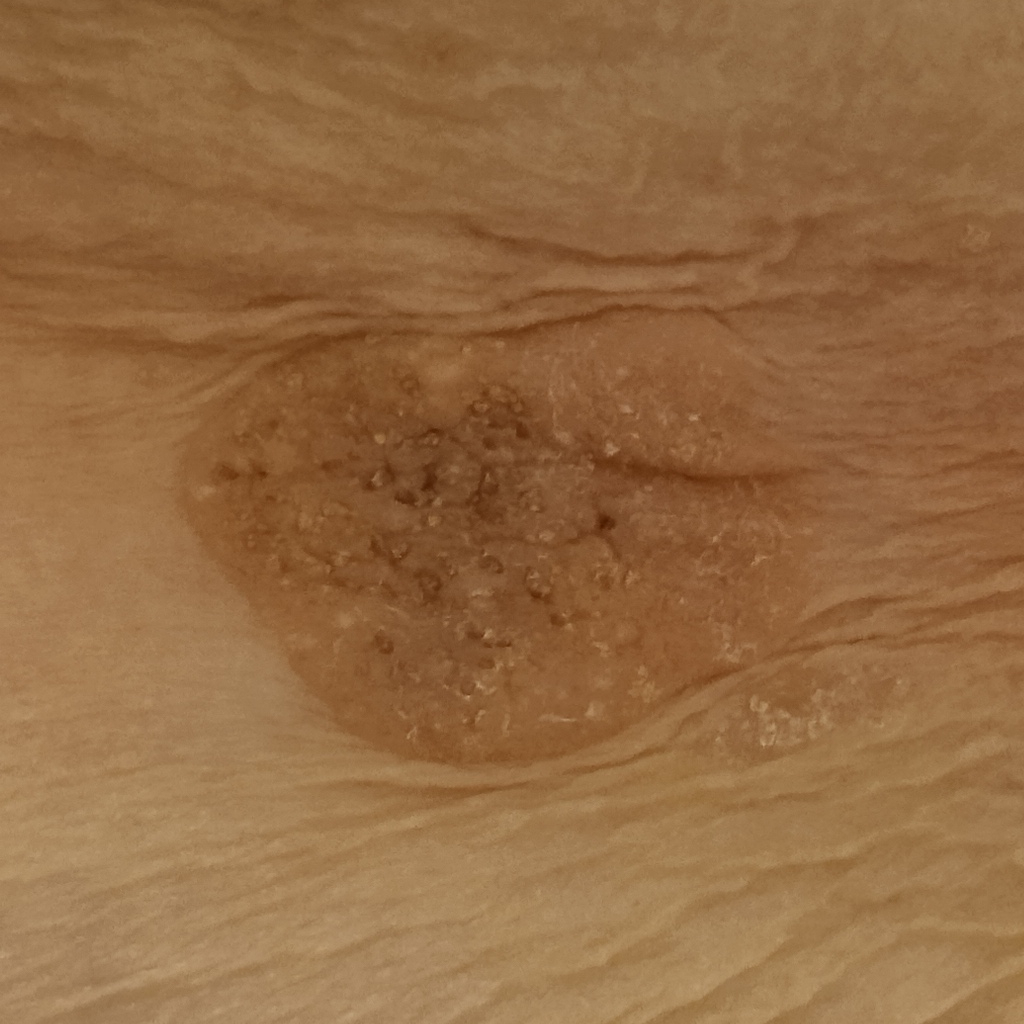On a questionnaire the patient reported no sunbed use. A female patient 81 years of age. Collected as part of a research study, without a referral diagnosis. The patient says their skin reddens painfully with sun exposure. A clinical photograph showing a skin lesion. Measuring roughly 31 mm. Dermatologist review favored a seborrheic keratosis.